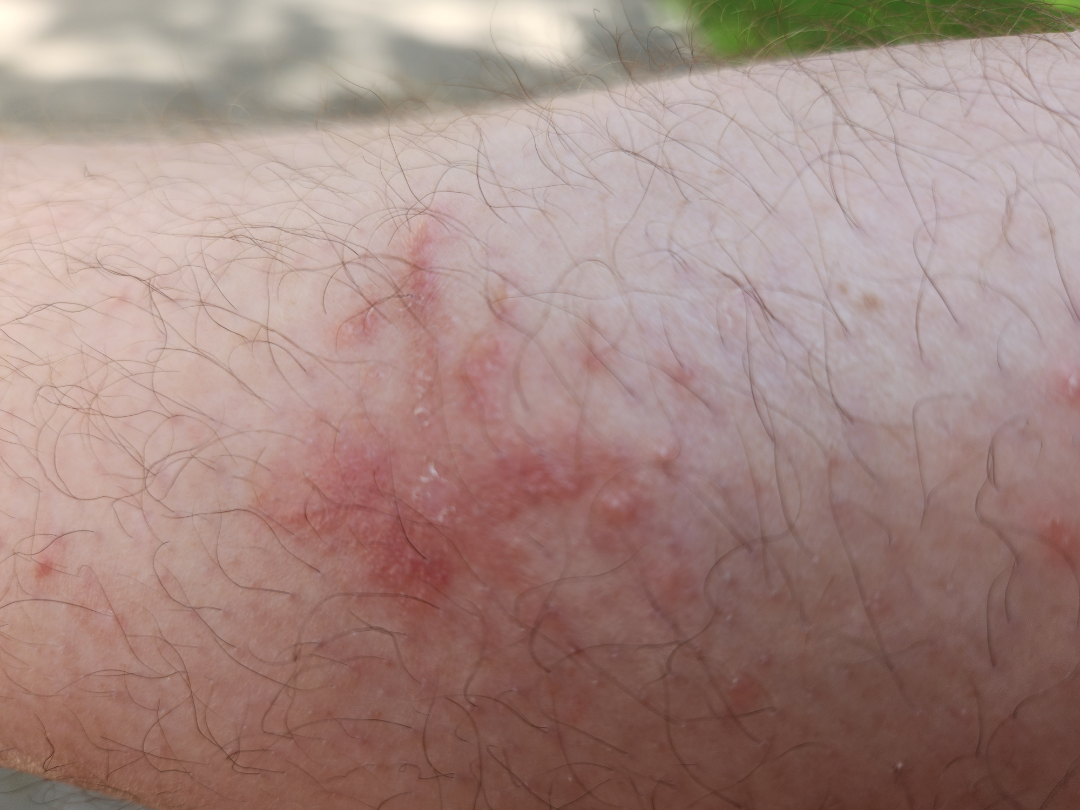Findings: The case was difficult to assess from the available photograph.